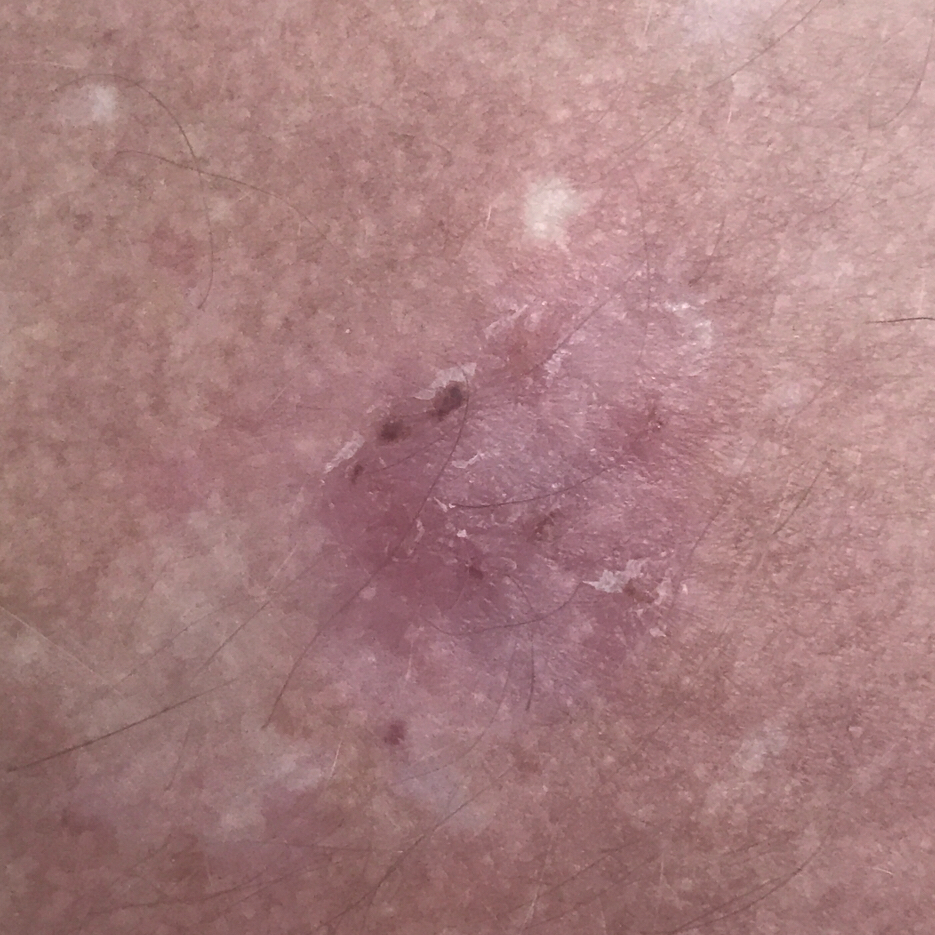The biopsy diagnosis was a basal cell carcinoma.